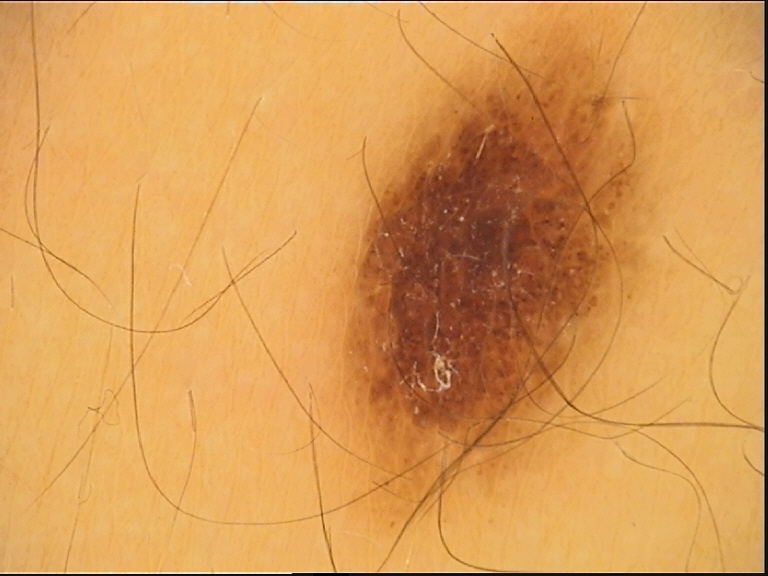Summary:
The morphology is that of a banal lesion.
Impression:
Consistent with a compound nevus.